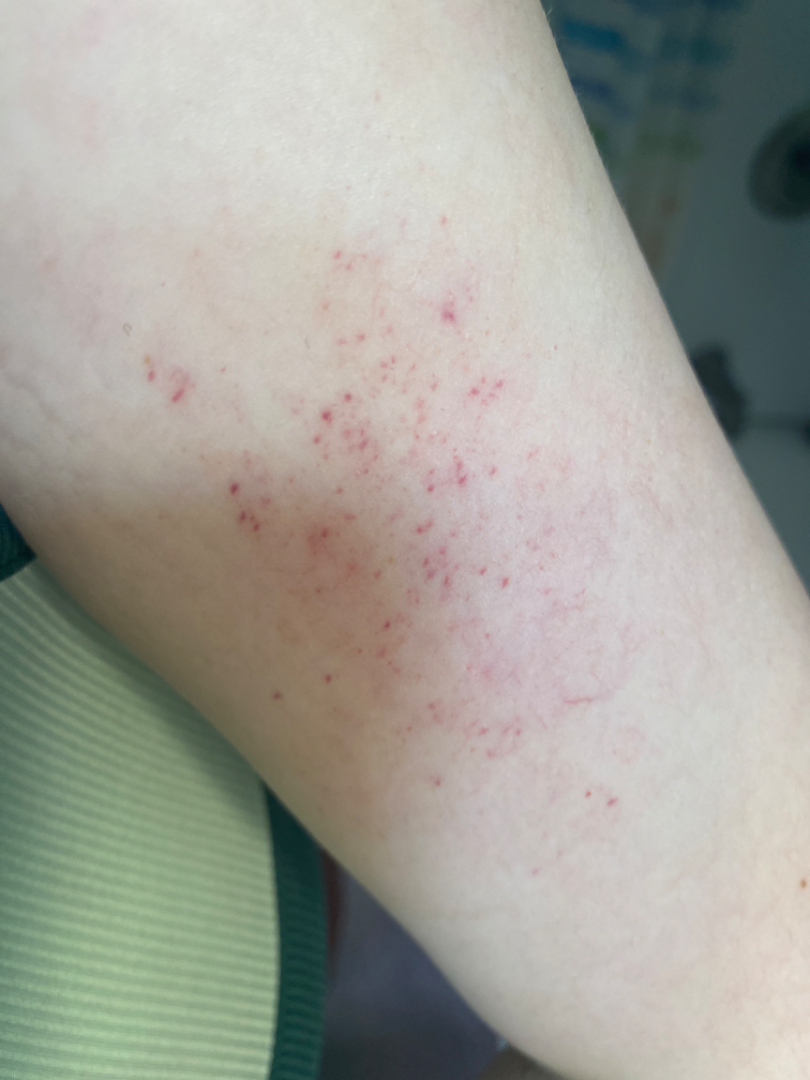{"differential": {"leading": ["petechiae"], "considered": ["Pigmented purpuric eruption", "Leukocytoclastic Vasculitis"]}}